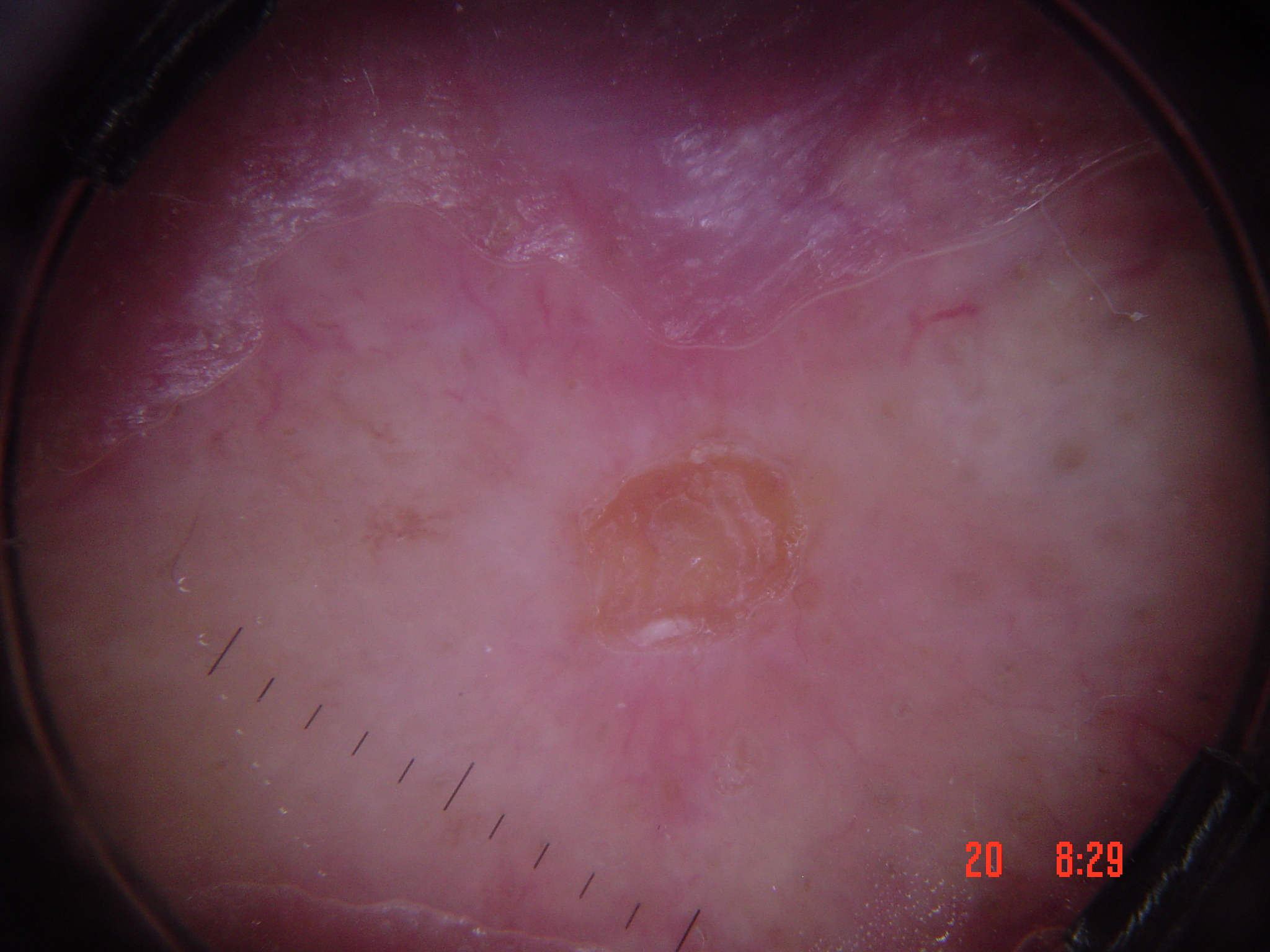A dermoscopy image of a single skin lesion. Histopathologically confirmed as a keratinocytic, malignant lesion — a squamous cell carcinoma.